A dermoscopic close-up of a skin lesion.
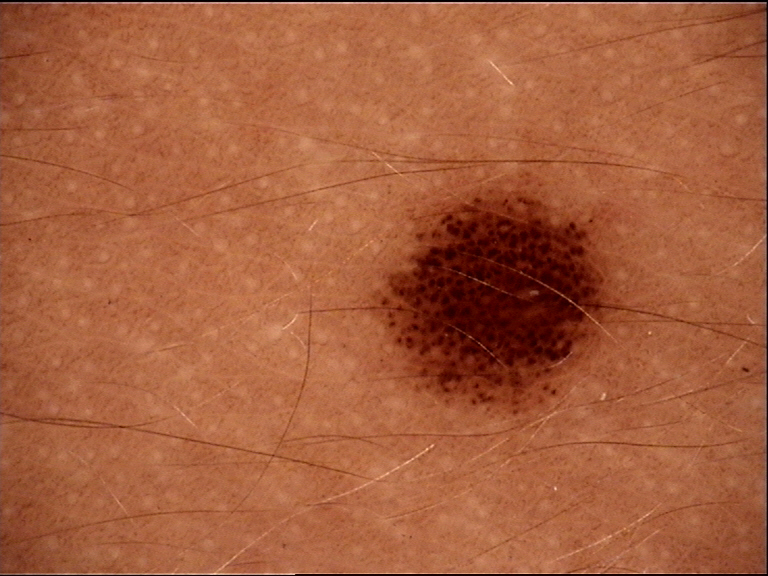Findings:
• classification — banal
• diagnosis — junctional nevus (expert consensus)